The patient describes having few moles overall · the patient says their skin tans without first burning · referred for assessment of suspected basal cell carcinoma · a female subject 60 years of age · dermoscopy of a skin lesion · on a questionnaire the patient reported a personal history of skin cancer and a personal history of cancer:
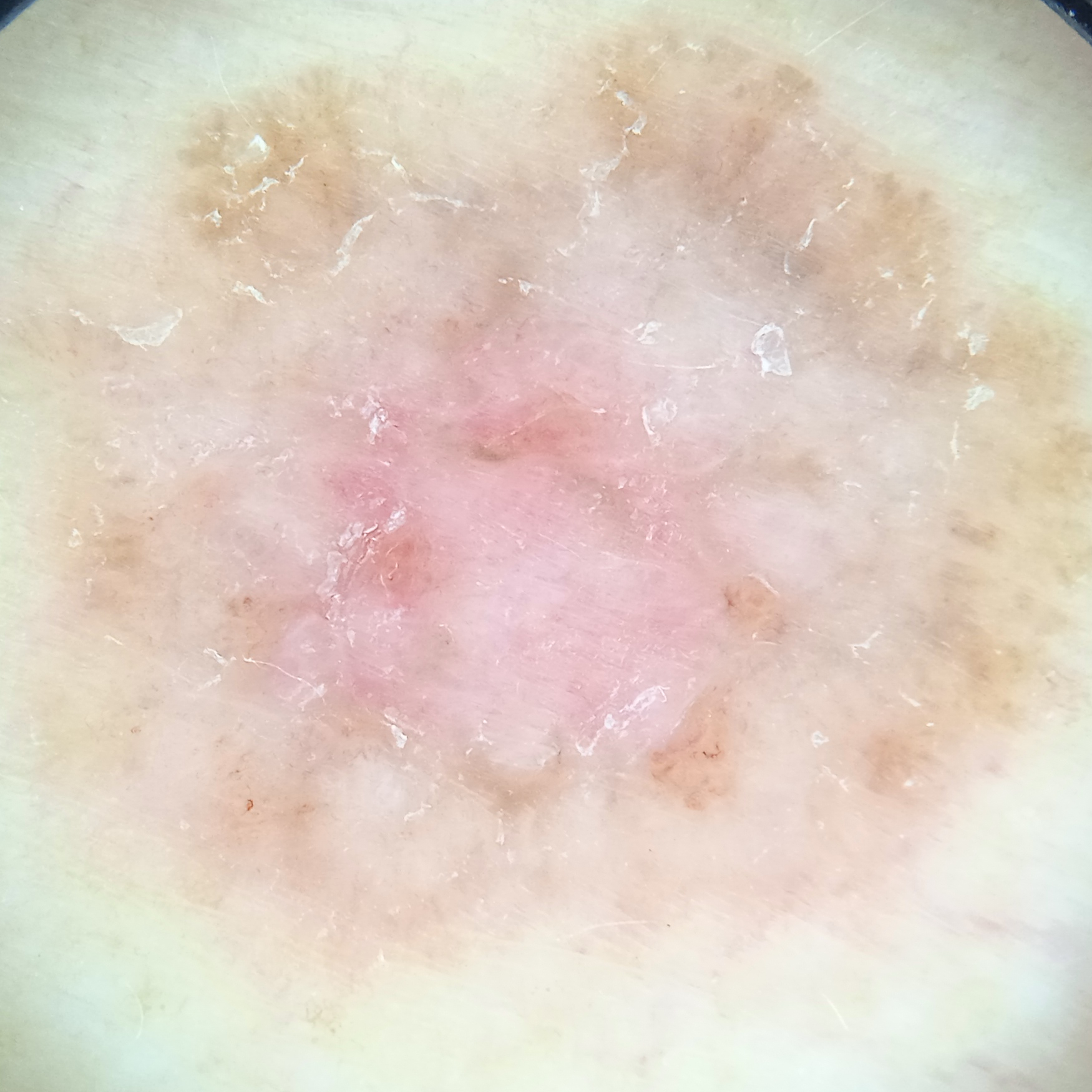site=the torso | size=13.2 mm | diagnosis=basal cell carcinoma (dermatologist consensus).